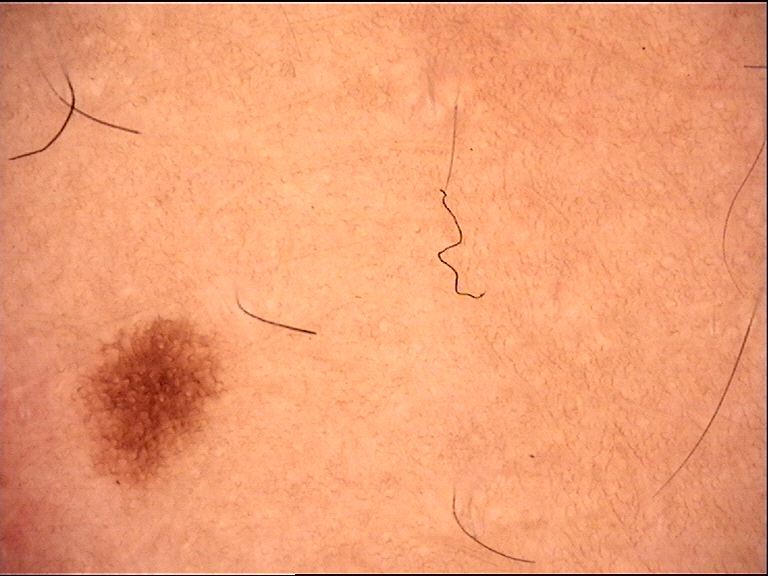A skin lesion imaged with a dermatoscope. Diagnosed as a banal lesion — a junctional nevus.